A close-up photograph. Reported duration is one to four weeks. No constitutional symptoms were reported. Reported lesion symptoms include itching, enlargement and bothersome appearance. Self-categorized by the patient as a rash. Texture is reported as raised or bumpy:
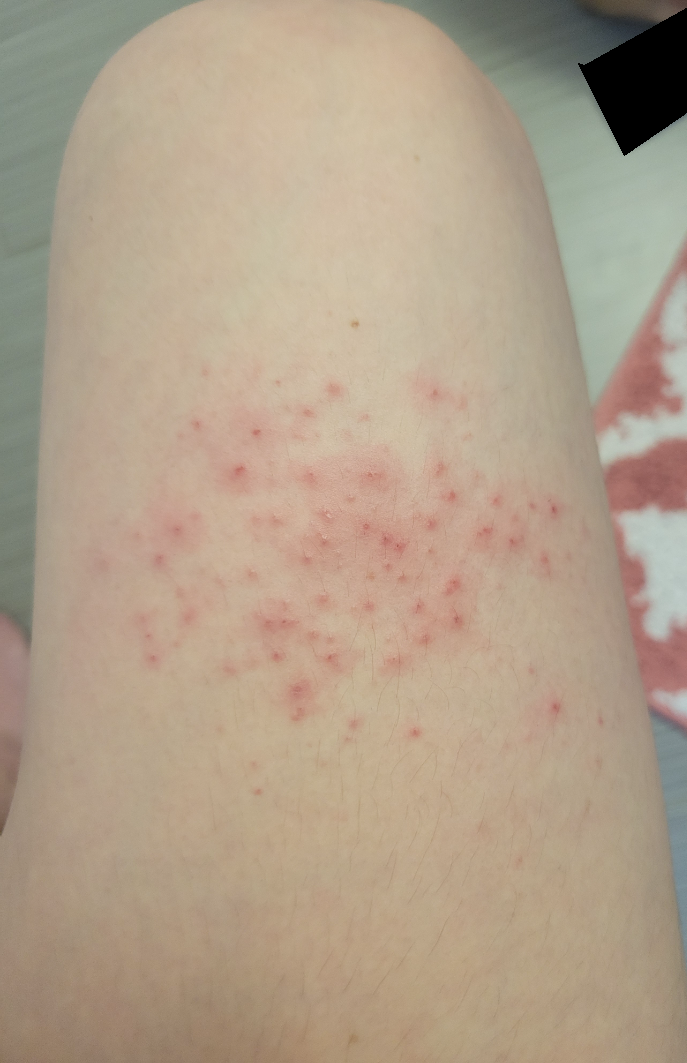Findings:
On remote dermatologist review, Dermatitis herpetiformis and Folliculitis were considered with similar weight; with consideration of Eczema.